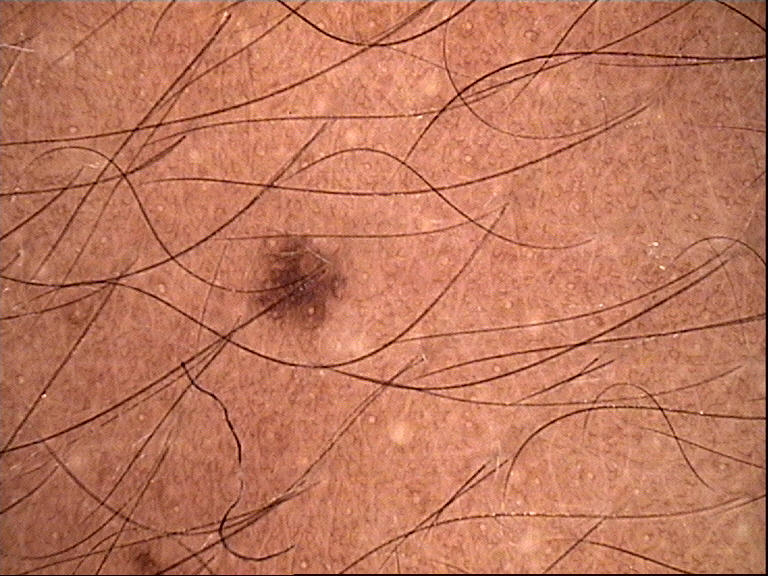Summary:
A dermoscopic image of a skin lesion.
Conclusion:
Classified as a banal lesion — a junctional nevus.